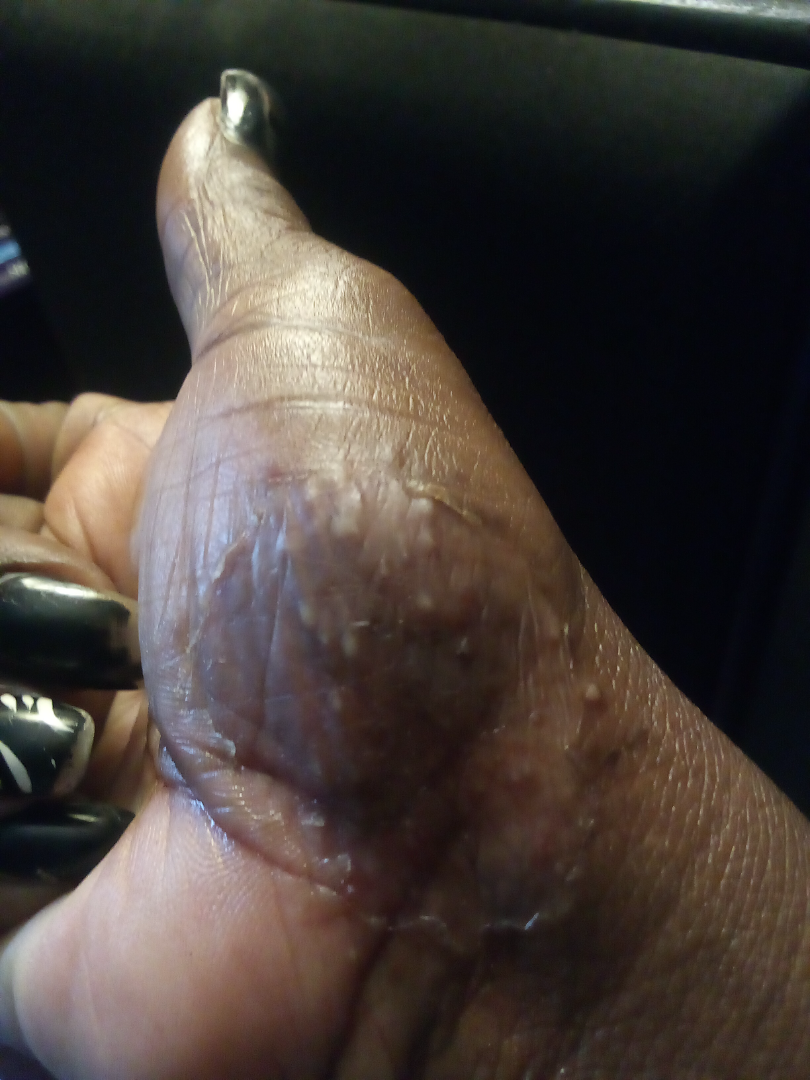photo taken=close-up
diagnostic considerations=Impetigo and Psoriasis were considered with similar weight; lower on the differential is Tinea